A dermoscopic close-up of a skin lesion.
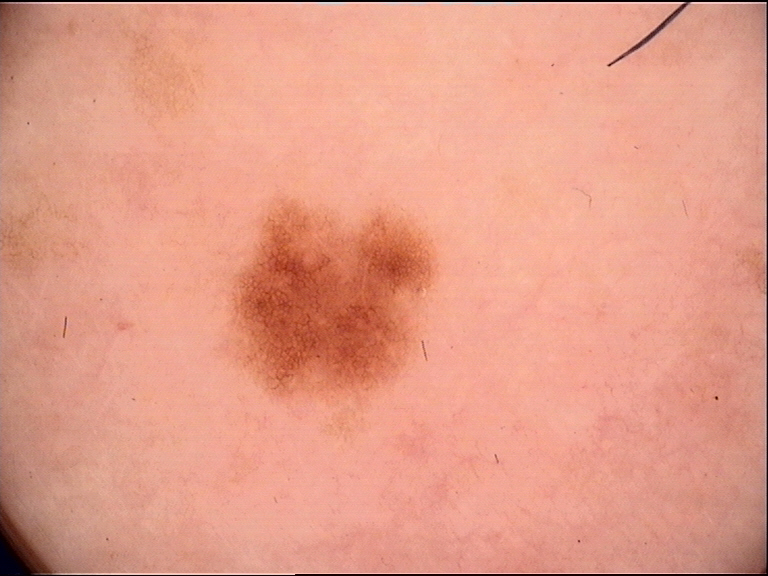The diagnostic label was a banal lesion — a junctional nevus.